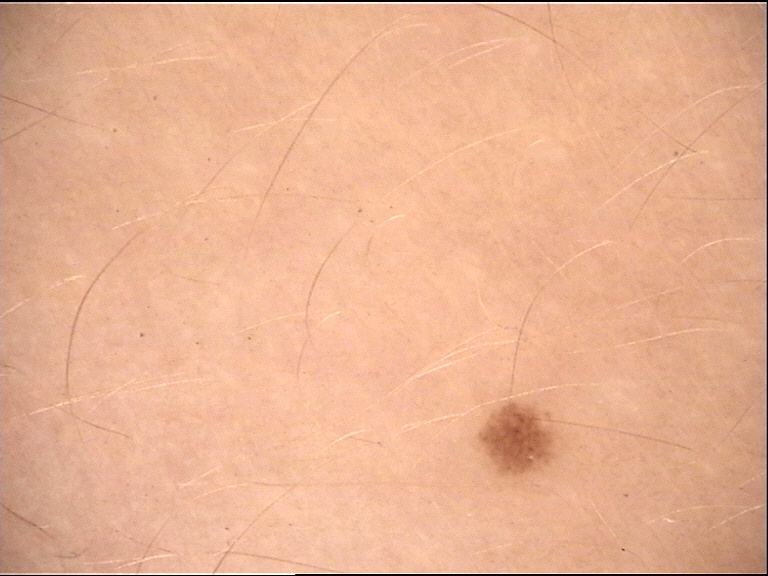* assessment: junctional nevus (expert consensus)